A dermoscopic photograph of a skin lesion.
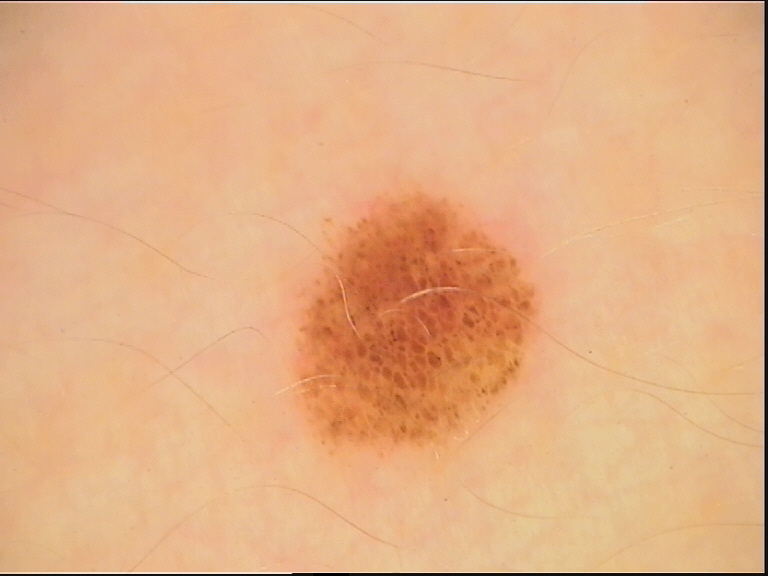Q: What is this lesion?
A: dysplastic compound nevus (expert consensus)